Recorded as skin type II; history notes prior skin cancer (patient or family), pesticide exposure, prior malignancy (patient or family), and no tobacco use; a female patient 24 years of age; a clinical photograph of a skin lesion: 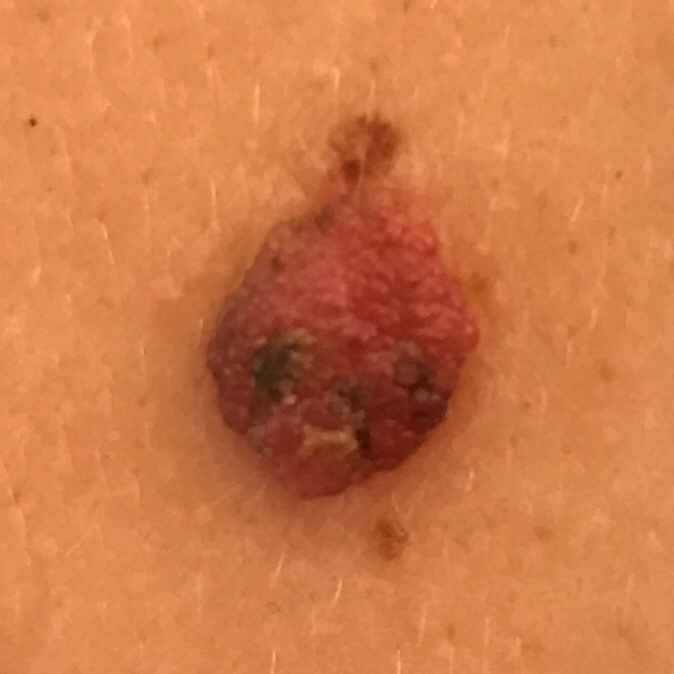Findings: Measuring about 11 × 9 mm. The patient reports that the lesion is elevated. Pathology: The biopsy diagnosis was a benign lesion — a nevus.